Located on the leg. Reported lesion symptoms include darkening, enlargement, itching and bothersome appearance. Texture is reported as rough or flaky and raised or bumpy. The patient reports the condition has been present for one to four weeks. This image was taken at a distance. The patient considered this skin that appeared healthy to them.
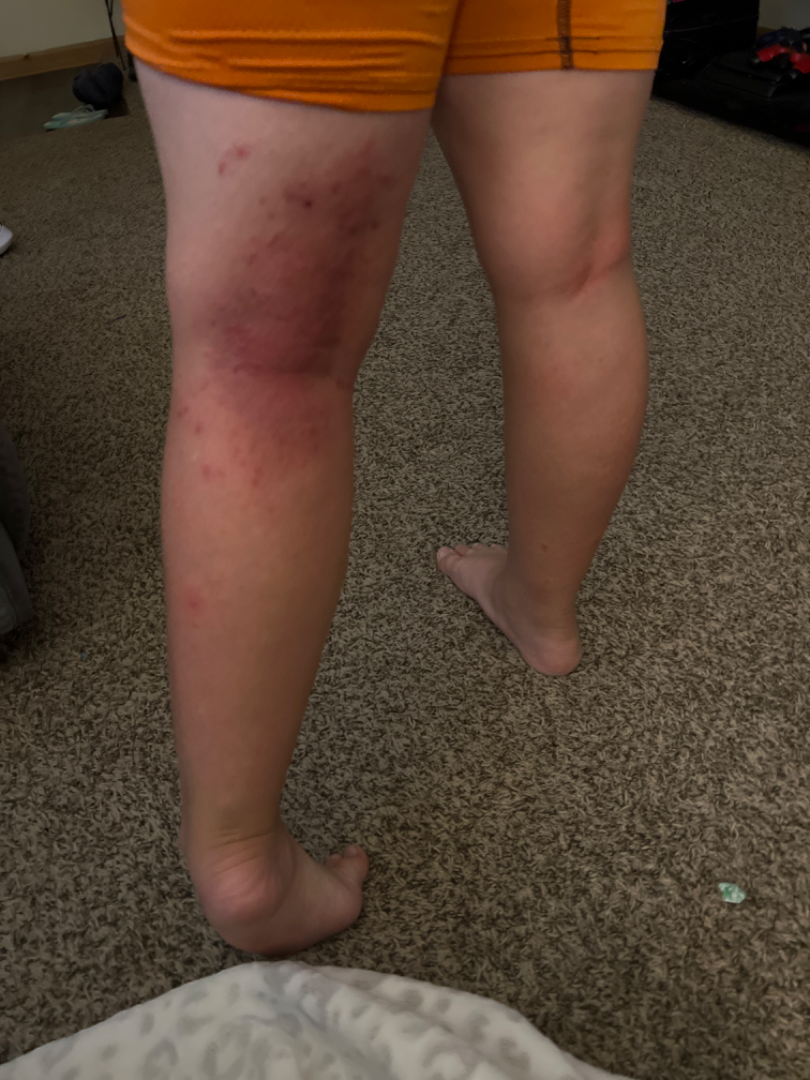dermatologist impression — Eczema (most likely); Allergic Contact Dermatitis (possible).